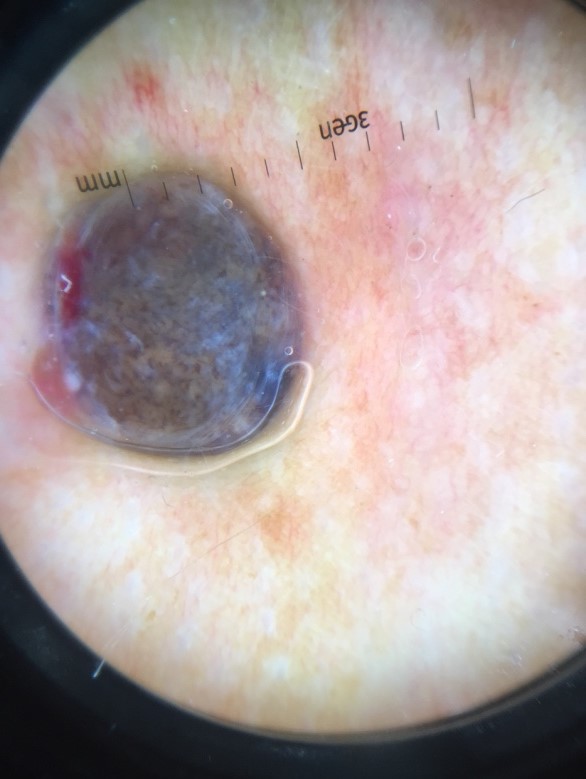Pathology:
The biopsy diagnosis was a malignant lesion — a melanoma.